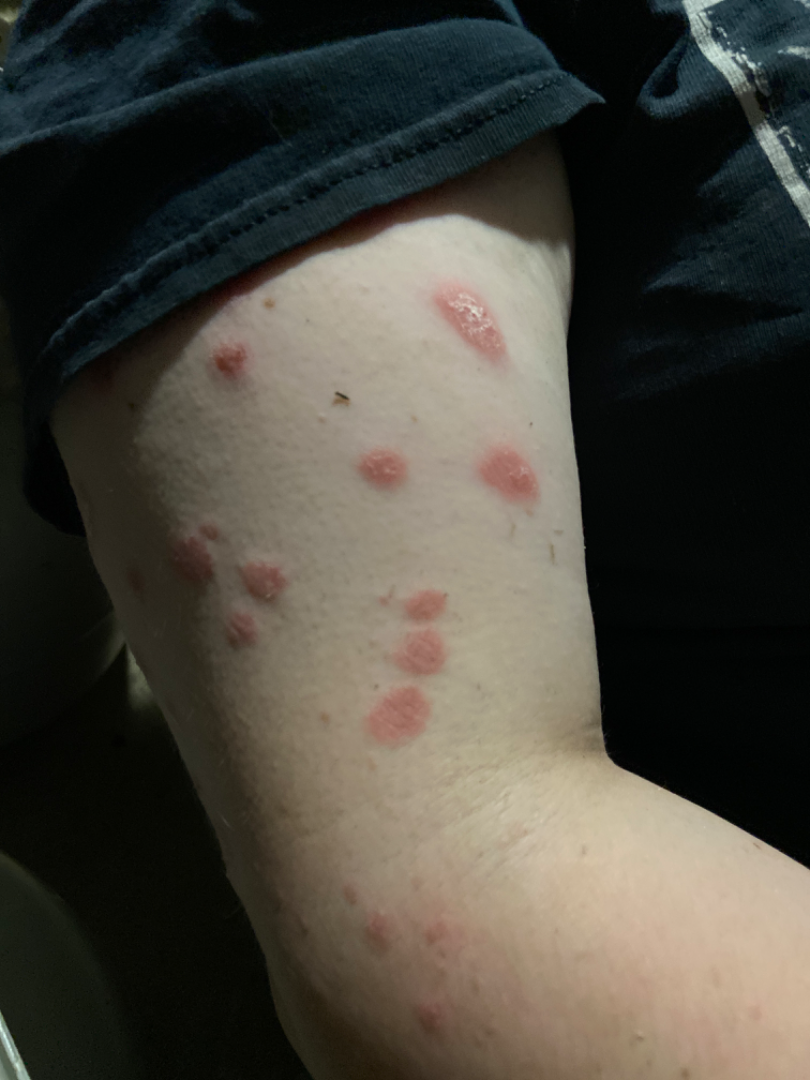contributor=female, age 18–29; anatomic site=arm and back of the torso; view=close-up; dermatologist impression=the differential, in no particular order, includes Psoriasis, Eczema and Allergic Contact Dermatitis.